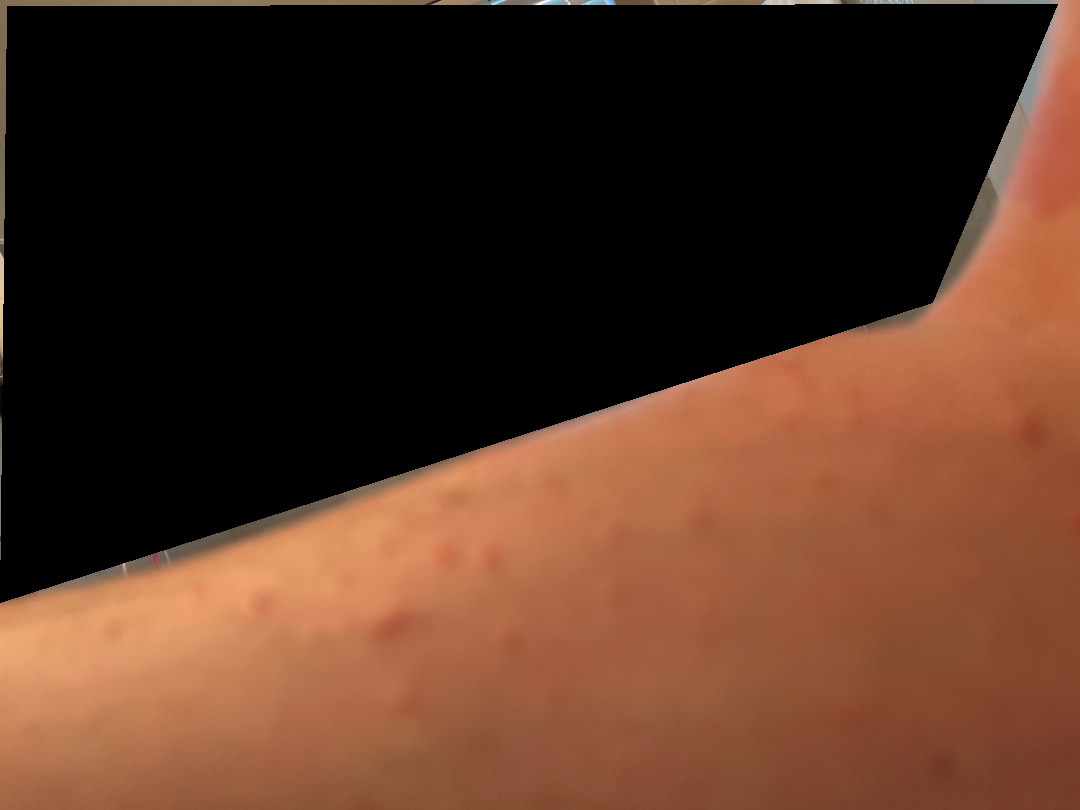Reported duration is one to four weeks. The lesion involves the arm, leg, back of the hand and head or neck. This image was taken at an angle. The lesion is described as rough or flaky, fluid-filled and raised or bumpy. On photographic review by a dermatologist: the primary impression is Allergic Contact Dermatitis; an alternative is Irritant Contact Dermatitis; a more distant consideration is Urticaria.